A dermoscopic image of a skin lesion:
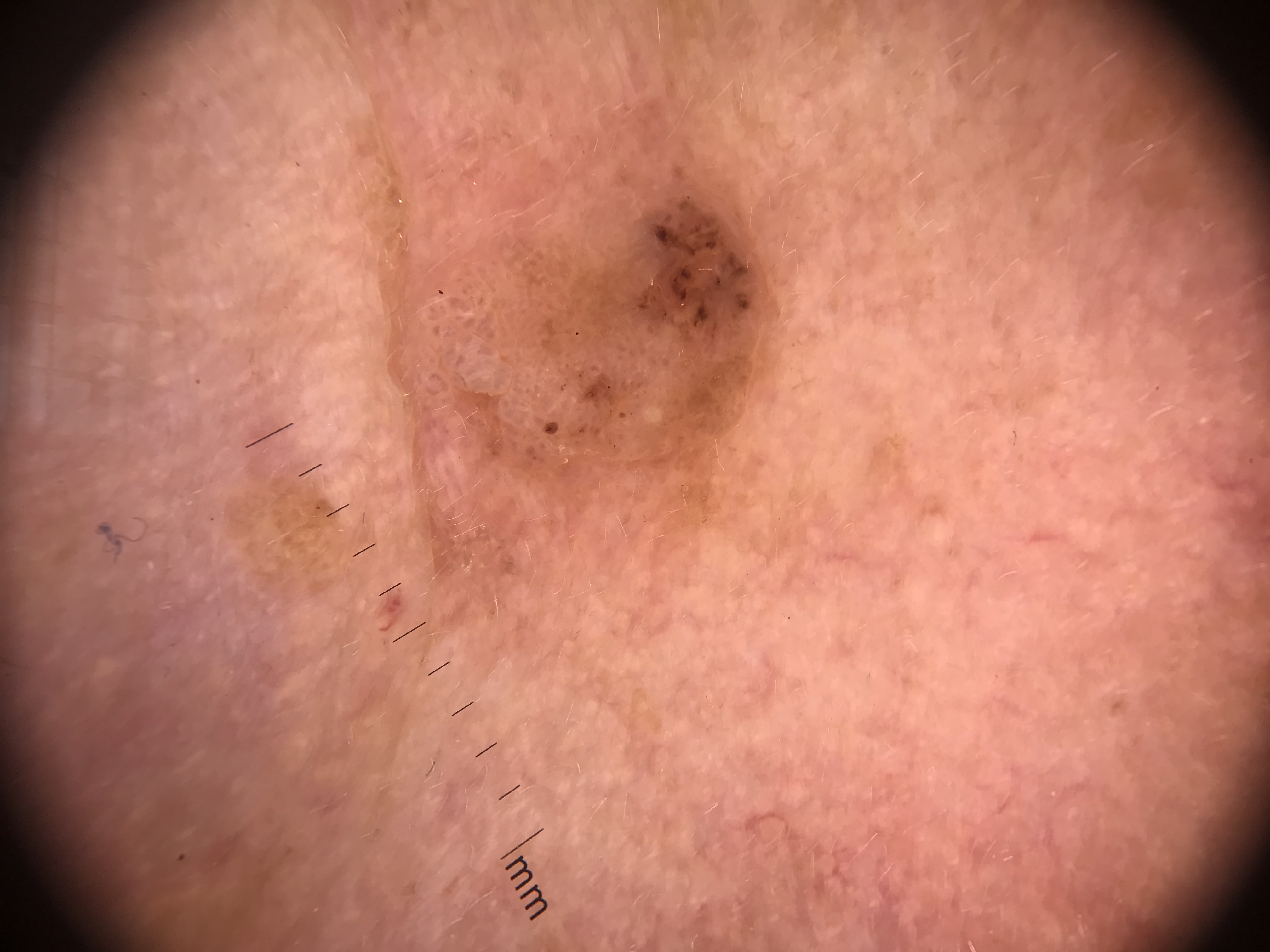The architecture is that of a keratinocytic lesion.
Classified as a seborrheic keratosis.